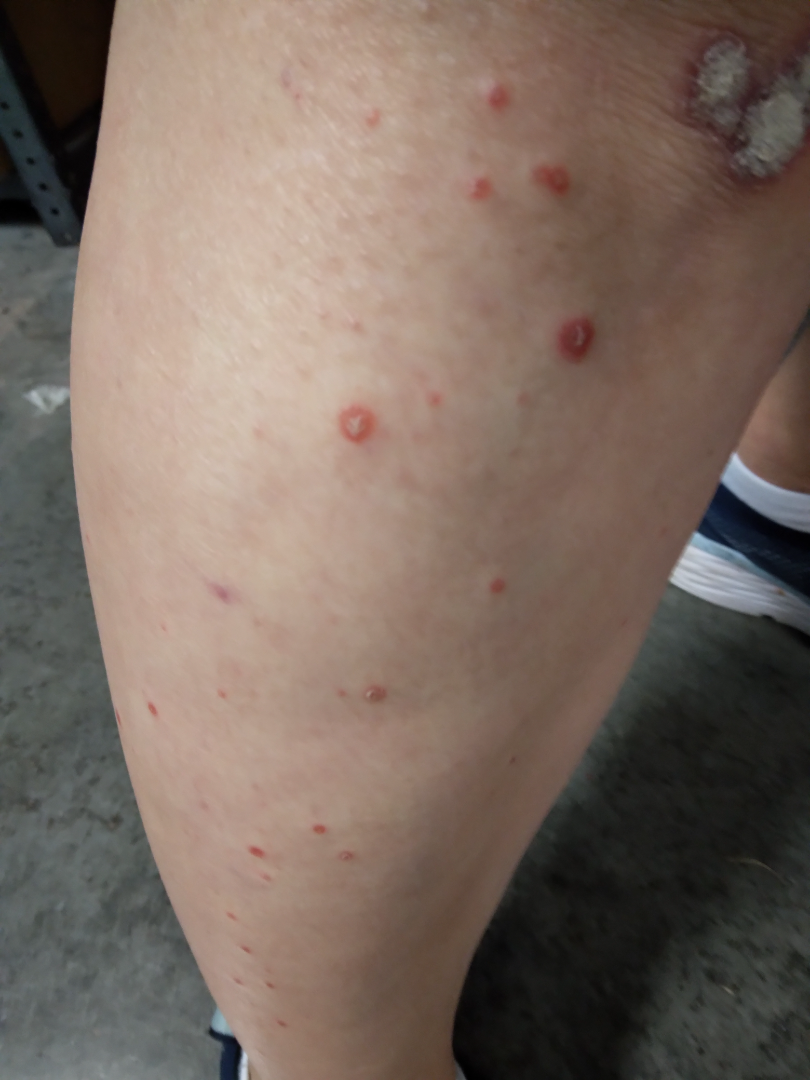| field | value |
|---|---|
| differential | in keeping with Psoriasis |